No associated systemic symptoms reported. Present for less than one week. The patient described the issue as a rash. The lesion involves the leg. The subject is female. Reported lesion symptoms include darkening and bothersome appearance. The lesion is described as rough or flaky and flat. A close-up photograph.
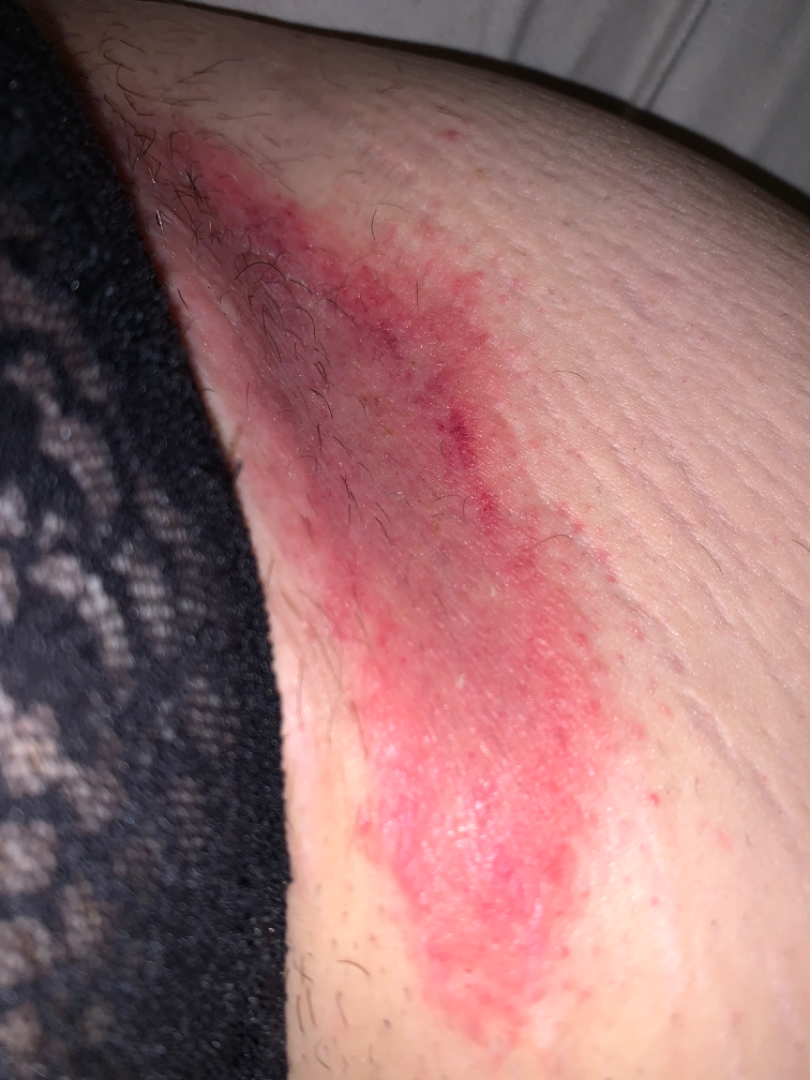differential diagnosis=three dermatologists independently reviewed the case: favoring Intertrigo; with consideration of Candida intertrigo; less probable is Irritant Contact Dermatitis; less likely is Allergic Contact Dermatitis